This image was taken at a distance, located on the top or side of the foot:
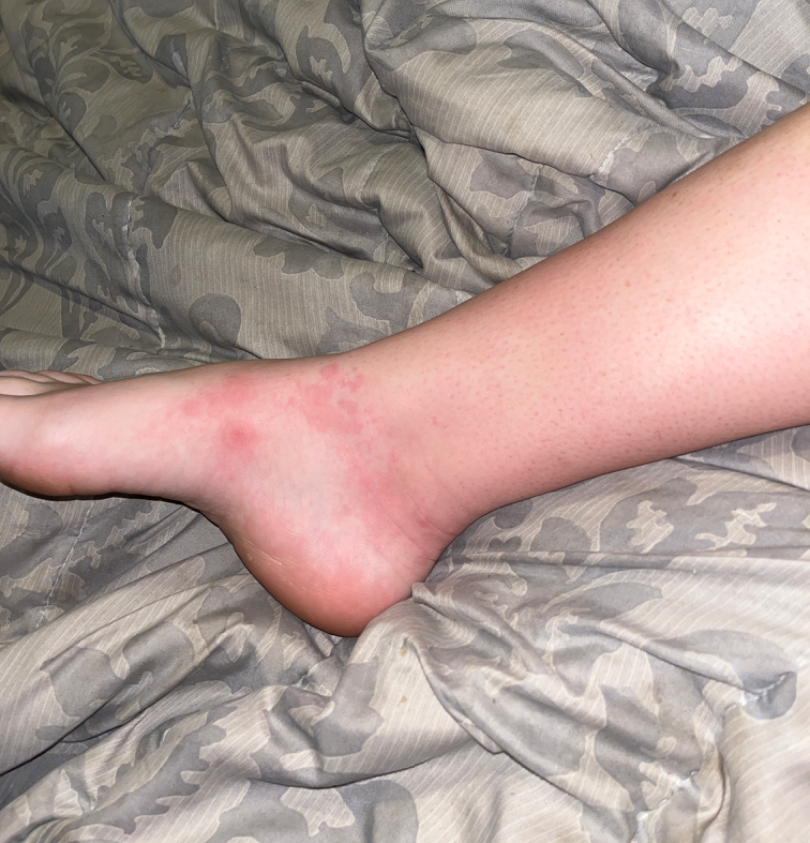assessment = could not be assessed
self-categorized as = a rash
skin tone = FST II; non-clinician graders estimated Monk skin tone scale 2–3
lesion texture = raised or bumpy